A skin lesion imaged with a dermatoscope: 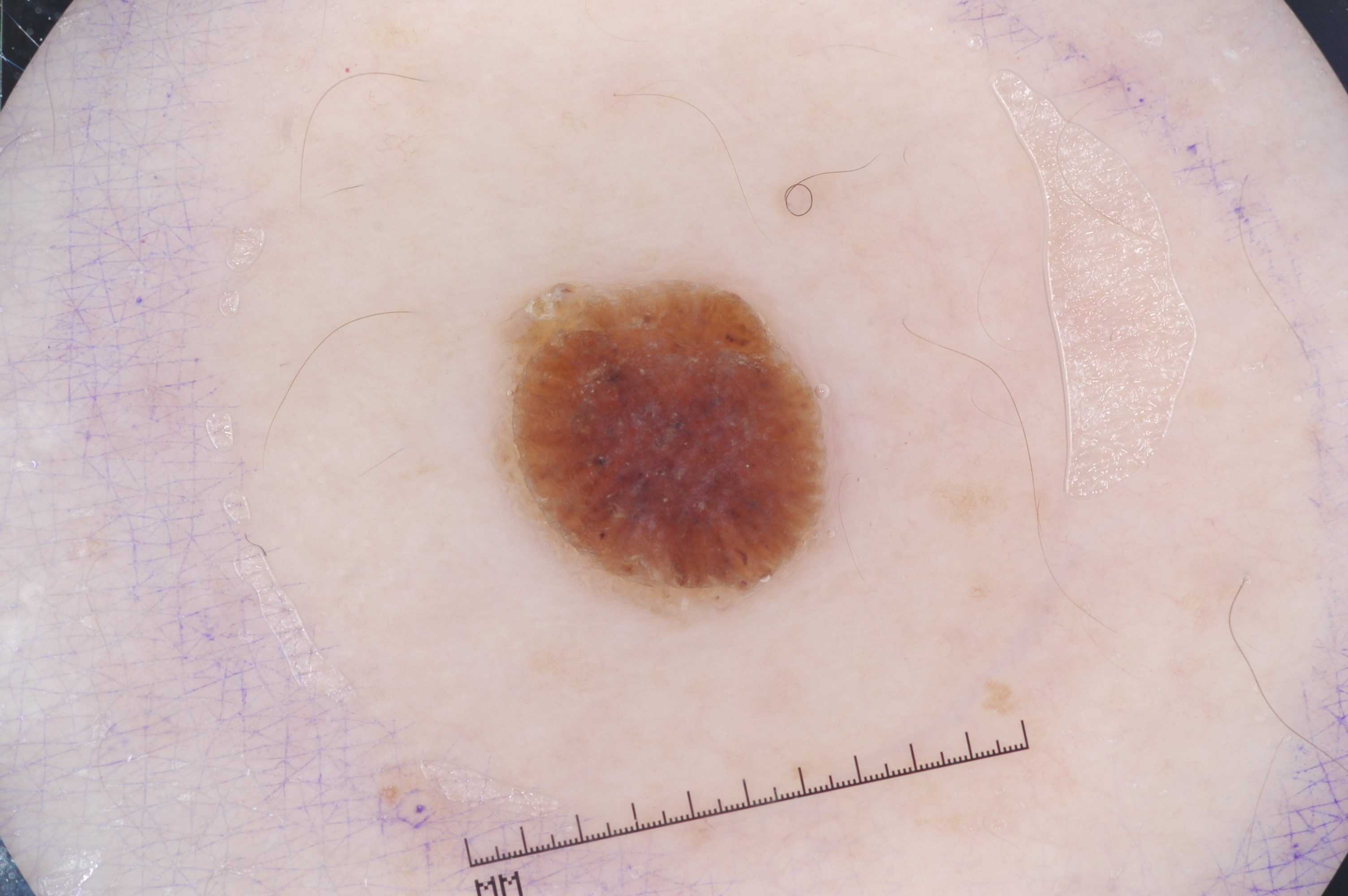Dermoscopic examination shows no pigment network, negative network, streaks, or milia-like cysts.
In (x1, y1, x2, y2) order, the lesion occupies the region bbox=[506, 280, 832, 609].
The lesion covers approximately 7% of the dermoscopic field.
The diagnostic assessment was a seborrheic keratosis, a keratinocytic lesion.